A dermatoscopic image of a skin lesion: 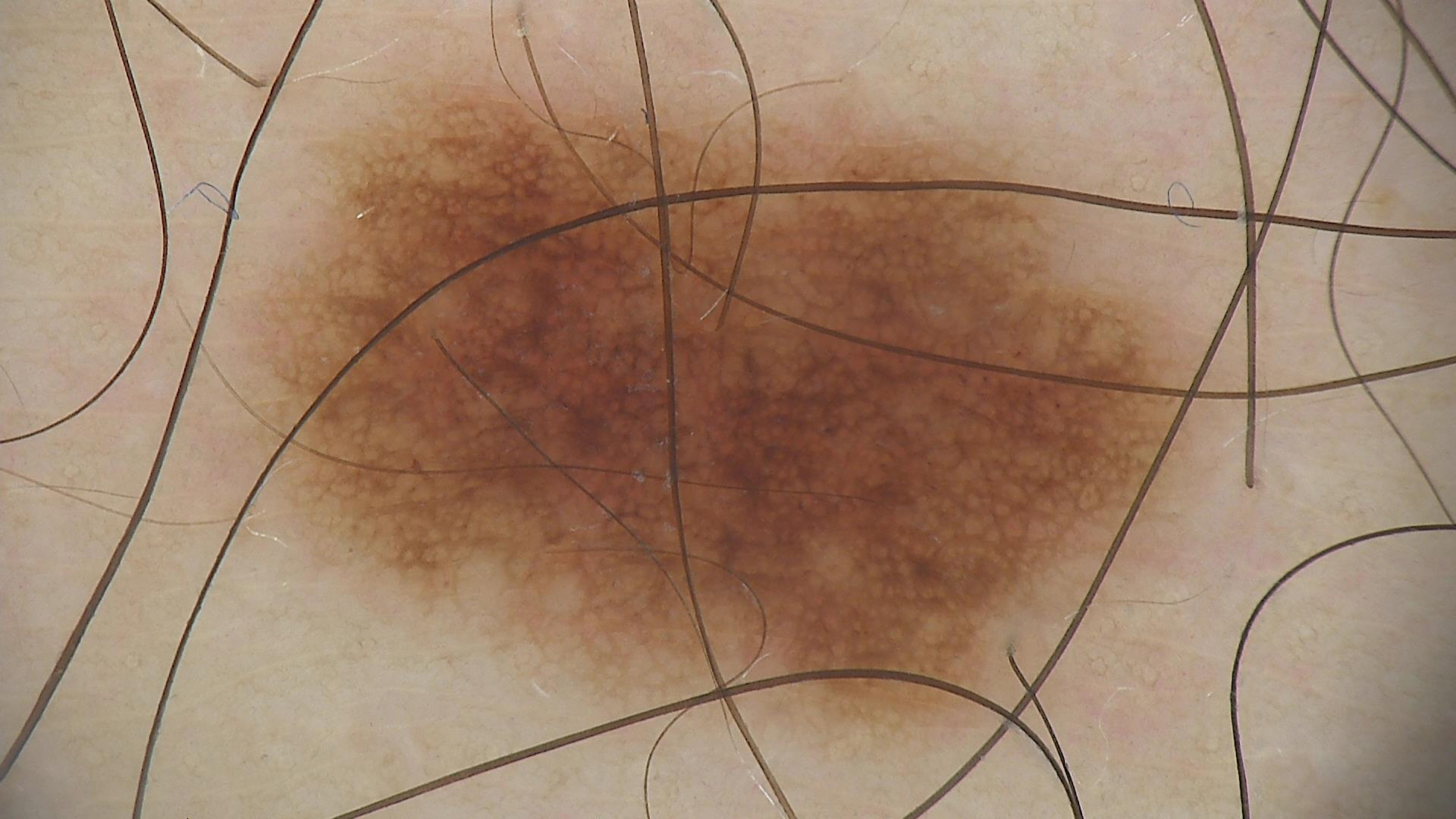diagnostic label: dysplastic junctional nevus (expert consensus).